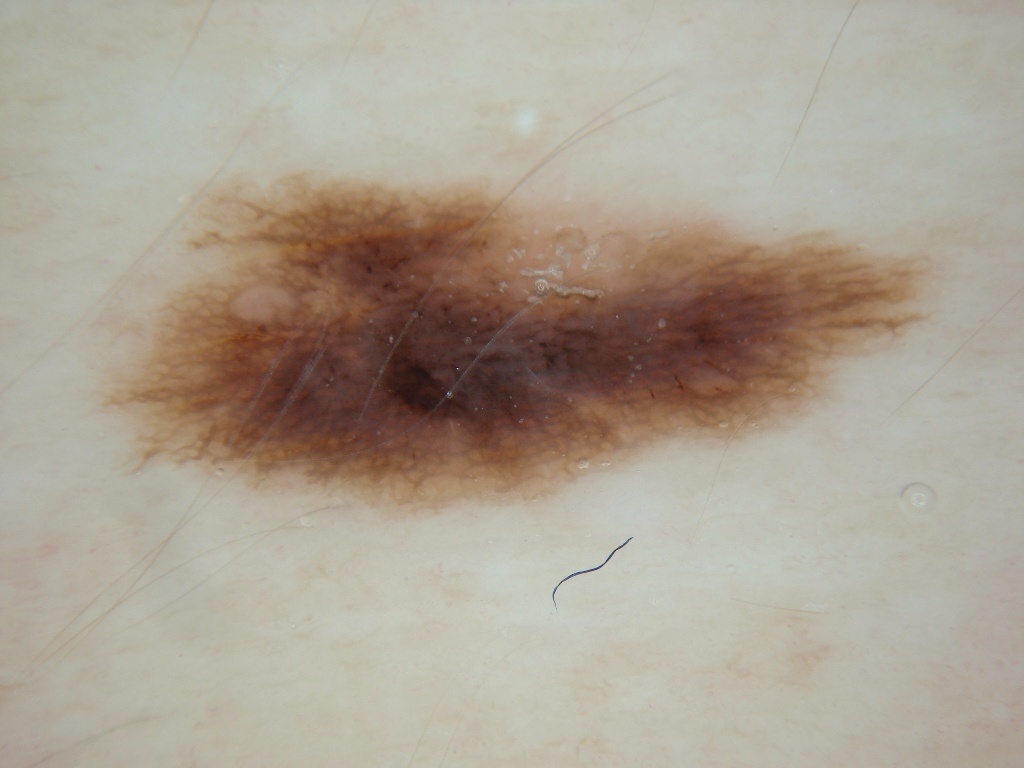A skin lesion imaged with a dermatoscope. With coordinates (x1, y1, x2, y2), the visible lesion spans box(102, 174, 945, 509). Dermoscopically, the lesion shows pigment network and streaks. A mid-sized lesion within the field. The lesion was assessed as a melanocytic nevus, a benign skin lesion.